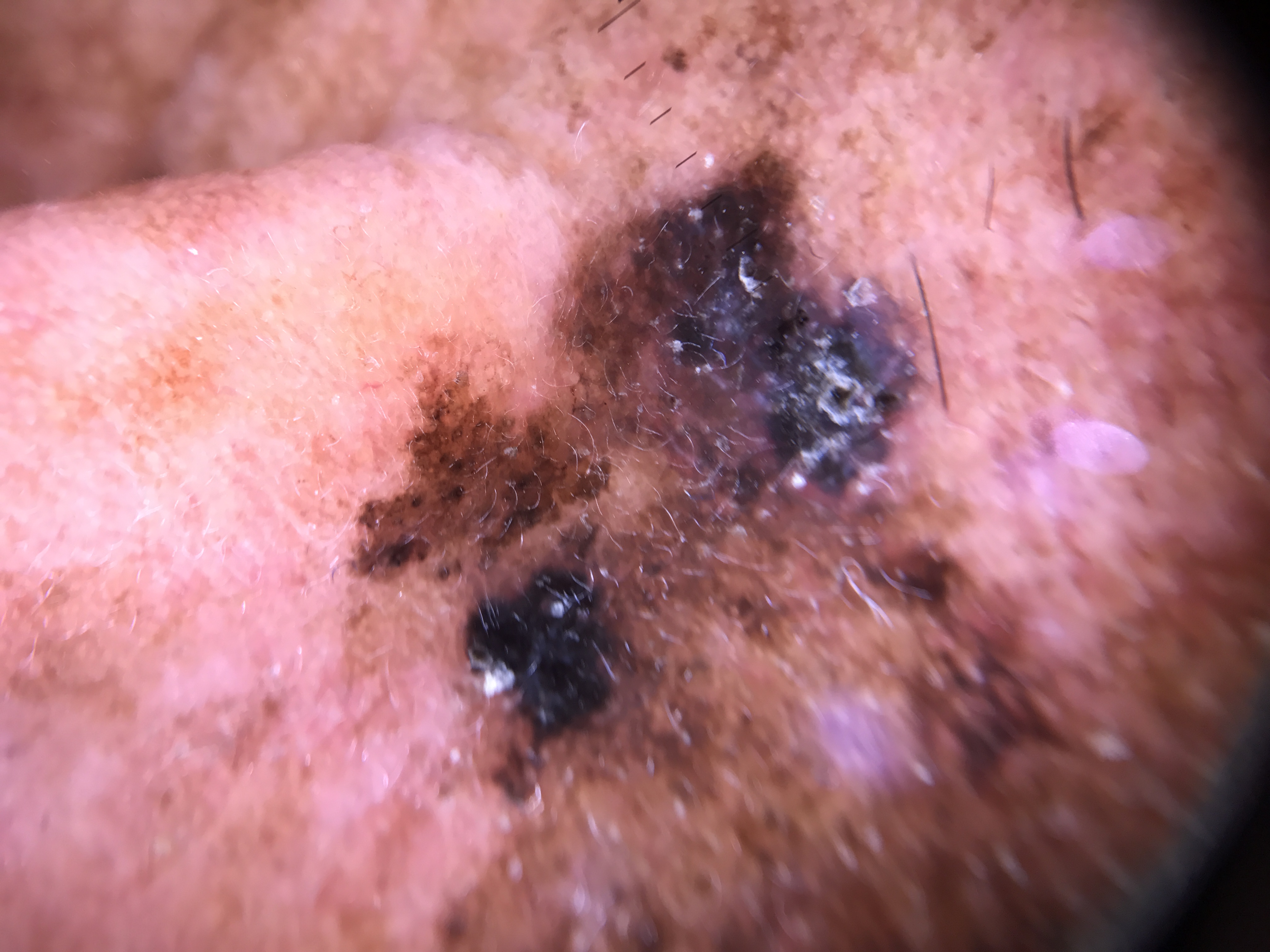- image — dermatoscopy
- pathology — lentigo maligna (biopsy-proven)